Located on the arm; this image was taken at an angle; male contributor, age 18–29: 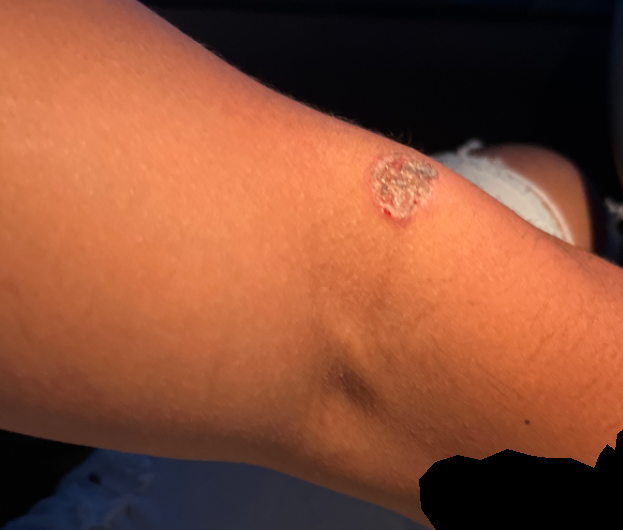symptoms: bleeding, darkening, enlargement, pain, itching and bothersome appearance
constitutional symptoms: none reported
symptom duration: one to three months
diagnostic considerations: Ecthyma (possible); Fungal dermatitis (possible); Cutaneous leishmaniasis (possible)